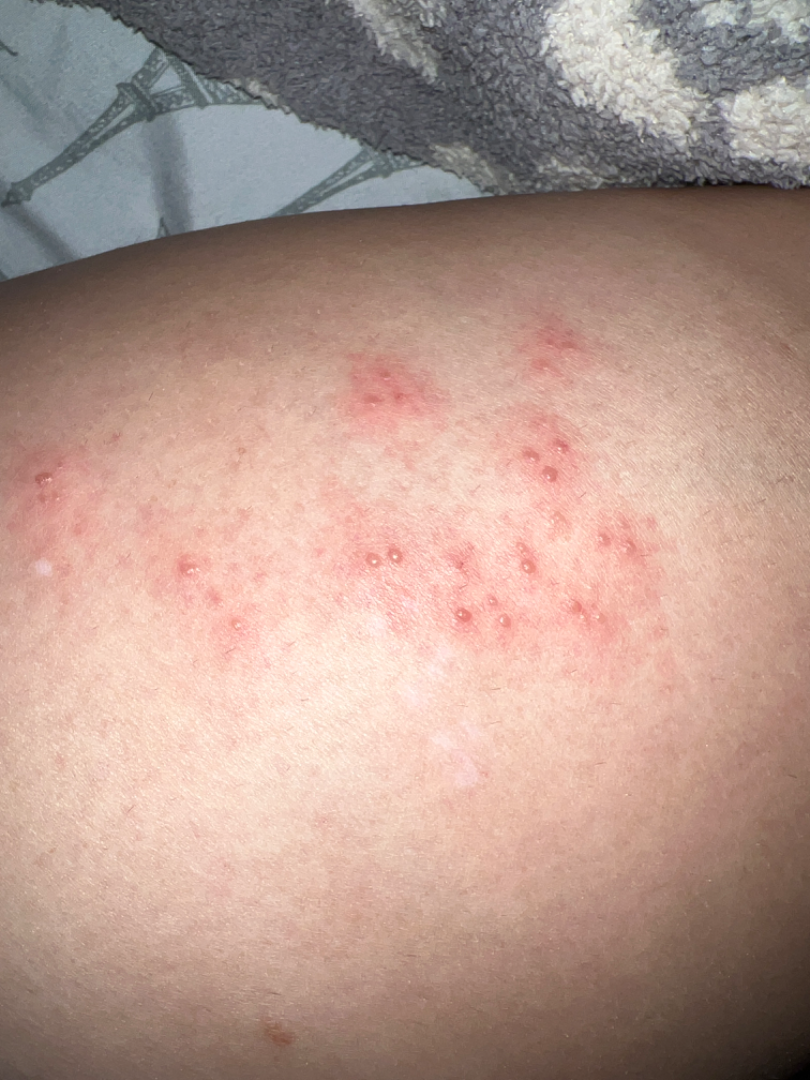| feature | finding |
|---|---|
| dermatologist impression | Herpes Zoster (favored); Insect Bite (lower probability); Molluscum Contagiosum (lower probability); Allergic Contact Dermatitis (lower probability) |